Close-up view, the patient considered this a rash, reported lesion symptoms include itching, the patient reported no systemic symptoms, texture is reported as flat: 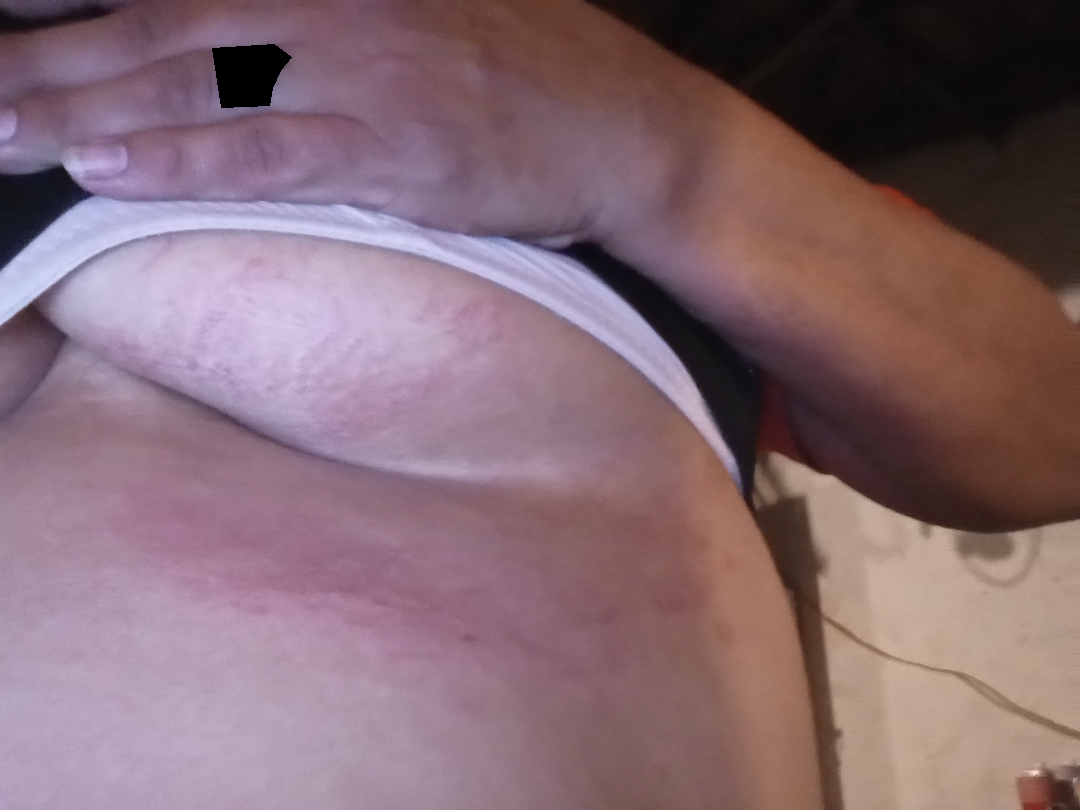Notes:
* assessment — not assessable